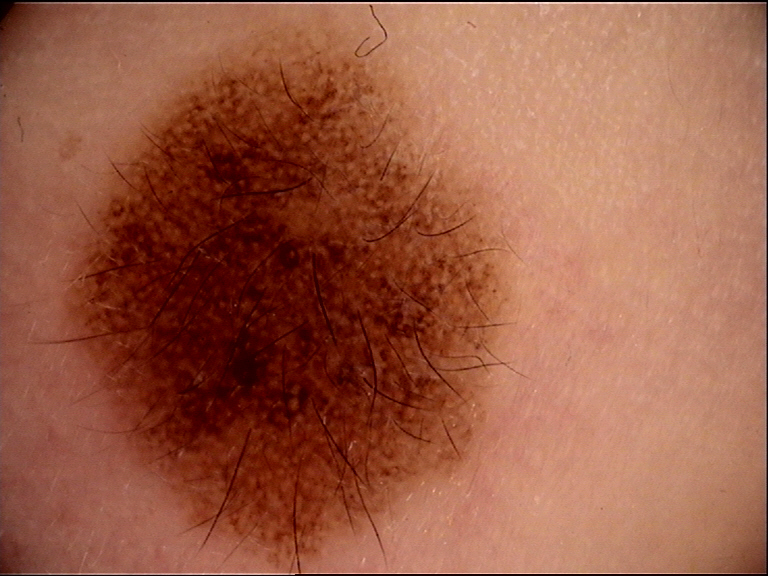image = dermoscopy
assessment = congenital compound nevus (expert consensus)